A dermoscopic image of a skin lesion:
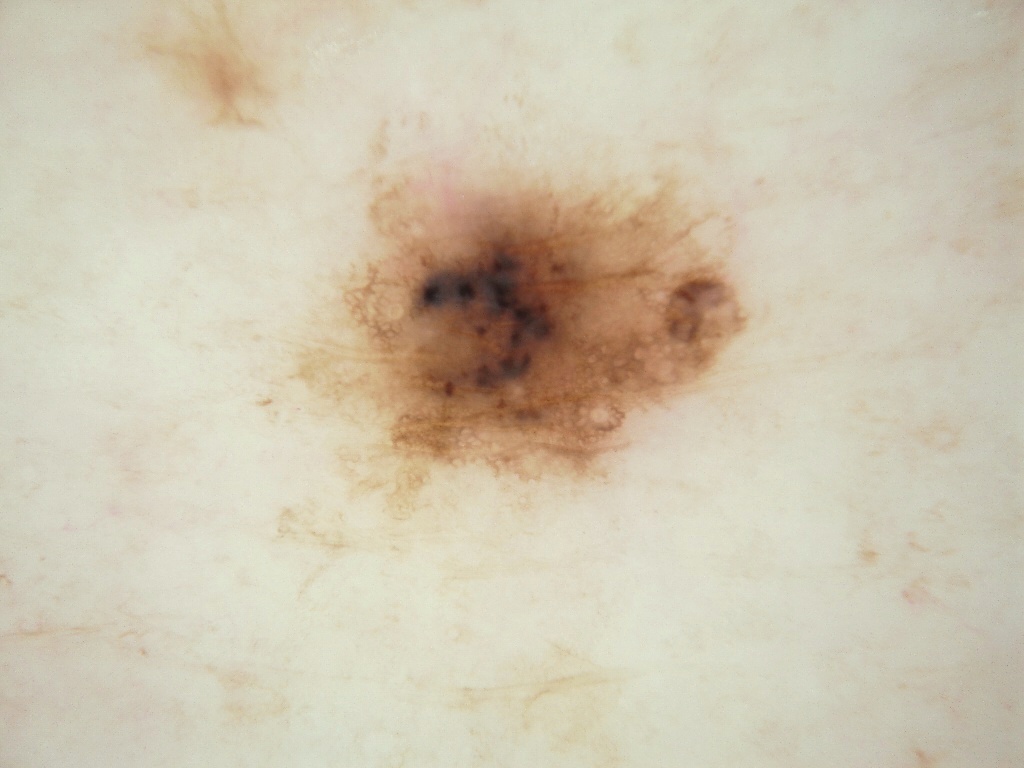The lesion covers approximately 23% of the dermoscopic field. Dermoscopic examination shows globules, with no streaks. In (x1, y1, x2, y2) order, the lesion occupies the region box(226, 92, 768, 545). Consistent with a benign skin lesion.